The photograph is a close-up of the affected area: 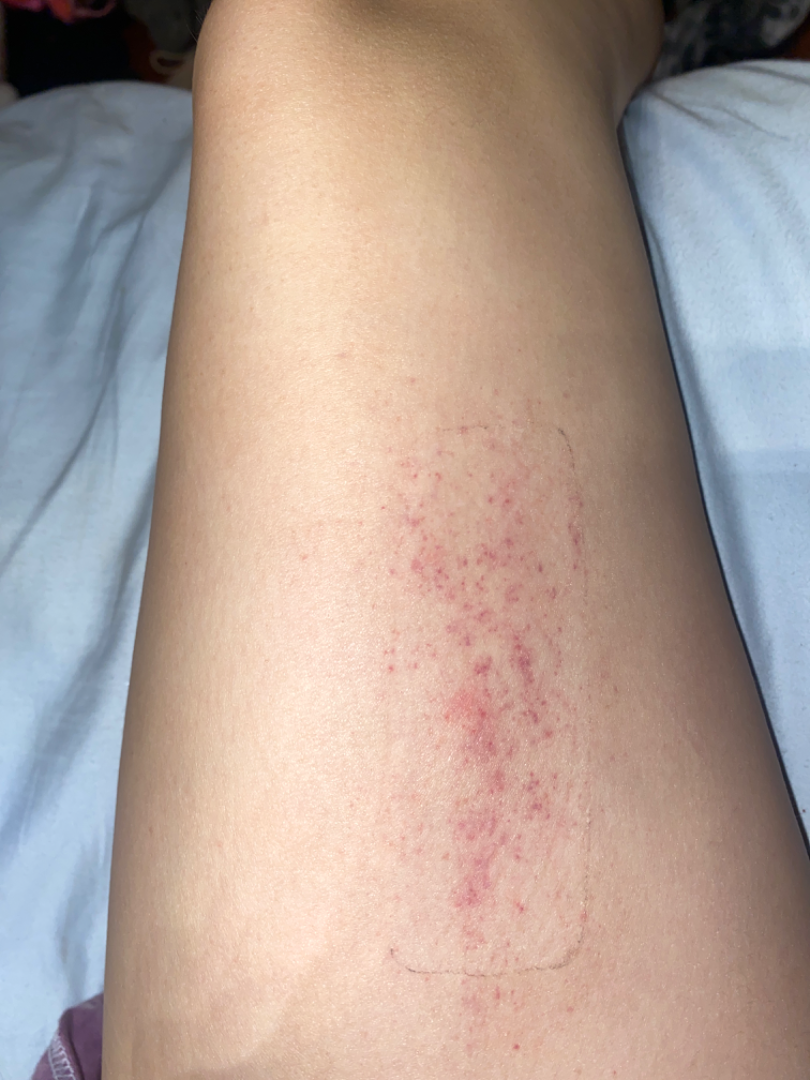assessment=the impression on review was Purpura.